Close-up view. No constitutional symptoms were reported. The patient reports the lesion is raised or bumpy. The lesion involves the leg. The patient did not report lesion symptoms. Reported duration is about one day:
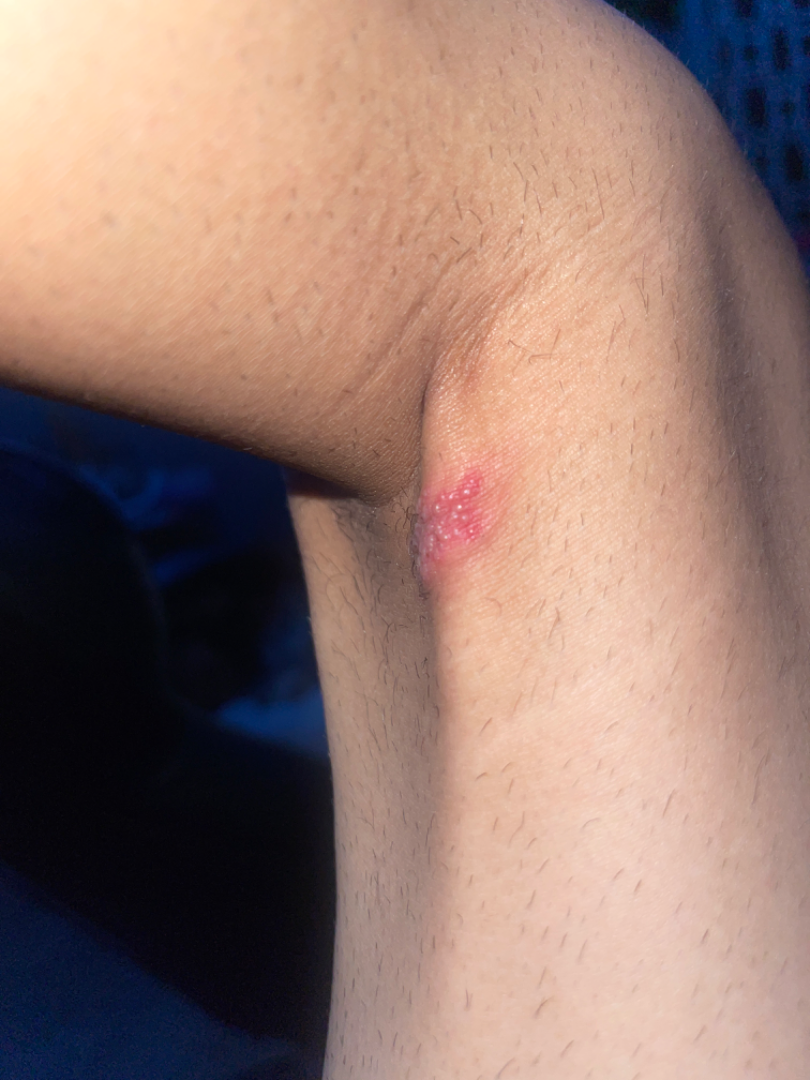impression — Herpes Simplex (most likely); Herpes Zoster (considered); Allergic Contact Dermatitis (less likely).